A dermoscopy image of a single skin lesion, the subject is a male roughly 70 years of age:
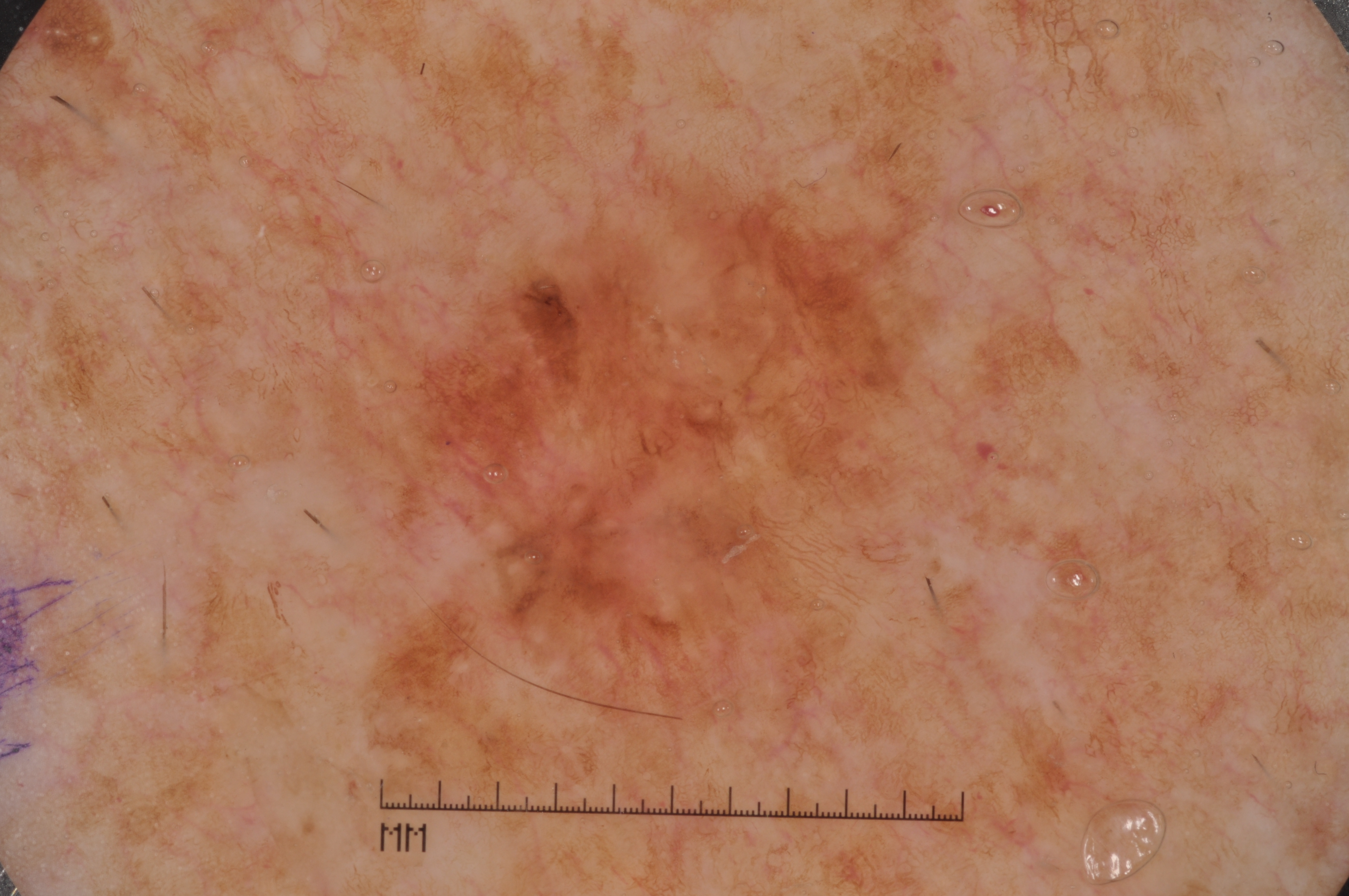Image and clinical context: A mid-sized lesion within the field. Dermoscopic review identifies pigment network. The visible lesion spans x1=333 y1=137 x2=996 y2=814. Conclusion: Confirmed on histopathology as a melanoma.